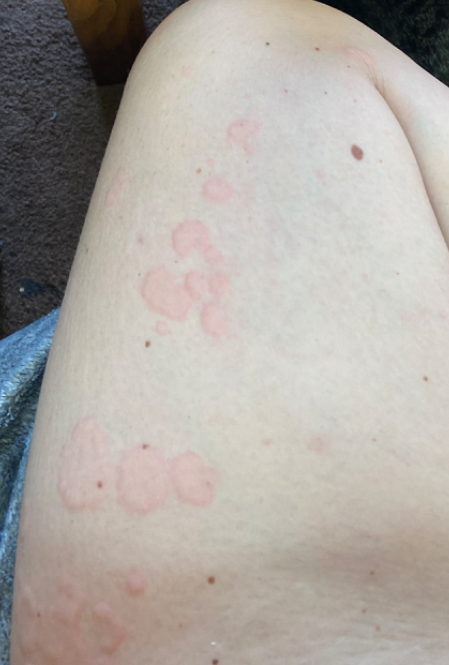Notes:
* anatomic site: front of the torso, head or neck, leg and arm
* lesion texture: raised or bumpy
* photo taken: at a distance
* systemic symptoms: fatigue
* present for: less than one week
* self-categorized as: a rash
* diagnostic considerations: the reviewer's impression was Urticaria